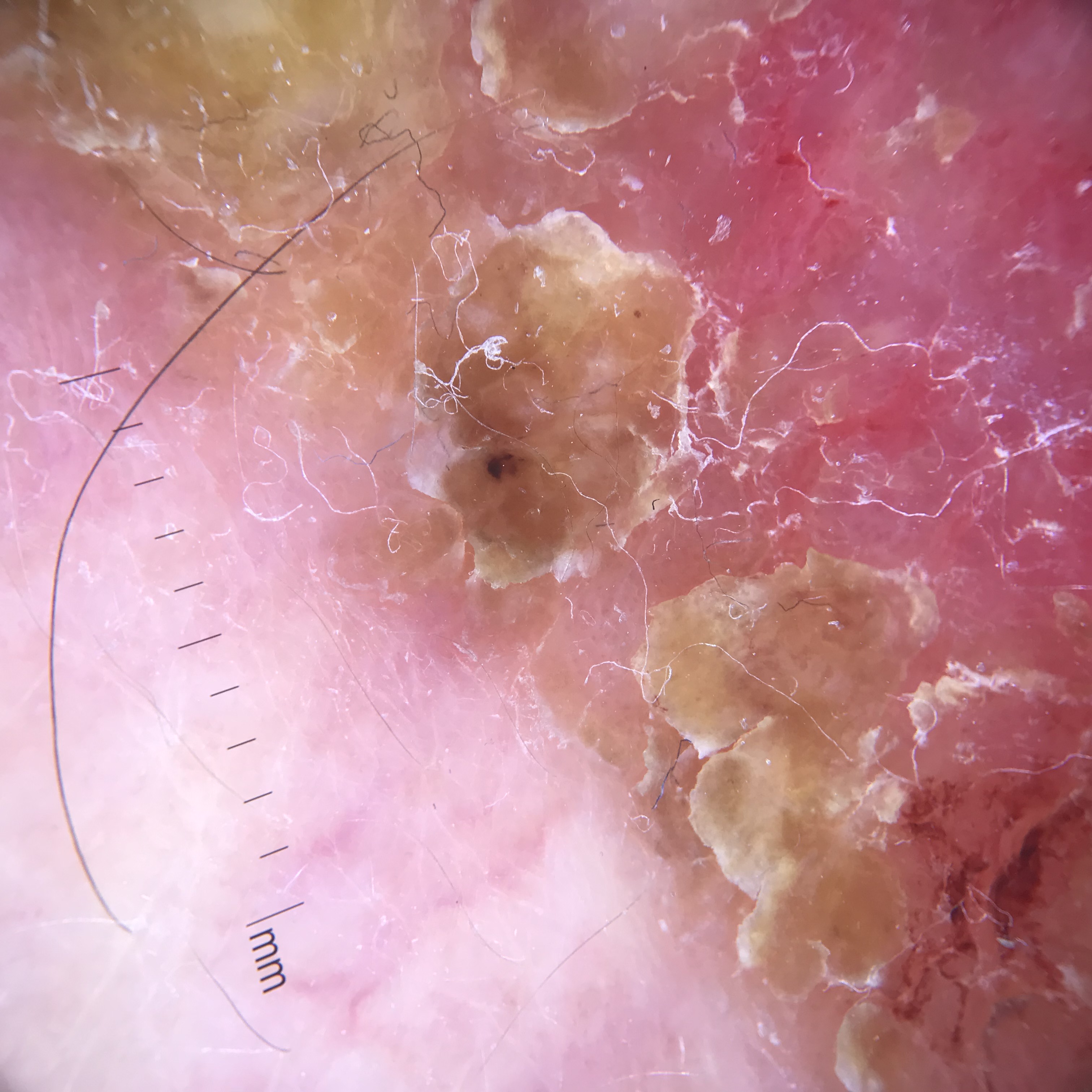<lesion>
  <image>dermoscopy</image>
  <diagnosis>
    <name>Bowen's disease</name>
    <code>bd</code>
    <malignancy>malignant</malignancy>
    <super_class>non-melanocytic</super_class>
    <confirmation>histopathology</confirmation>
  </diagnosis>
</lesion>